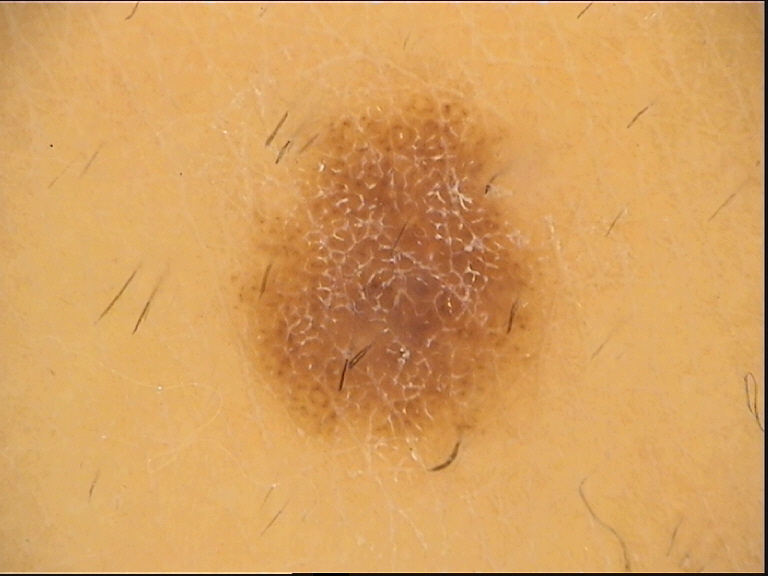imaging: dermoscopy; label: dysplastic junctional nevus (expert consensus).